The lesion involves the back of the torso. The photograph is a close-up of the affected area. The condition has been present for one to four weeks. The contributor reports the lesion is raised or bumpy and rough or flaky. The lesion is associated with bothersome appearance and itching: 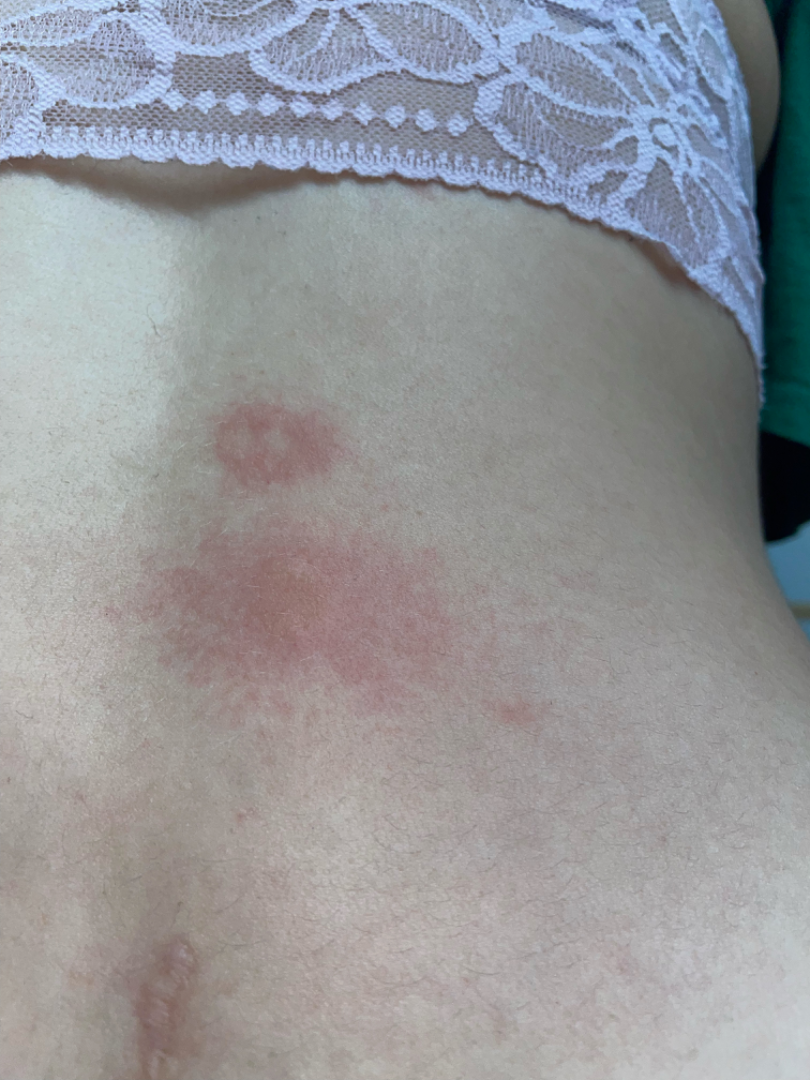Review: The reviewing clinician's impression was: consistent with Urticaria.